The patient considered this a rash. A close-up photograph. Present for less than one week. No relevant systemic symptoms. Located on the leg and arm. Symptoms reported: itching.
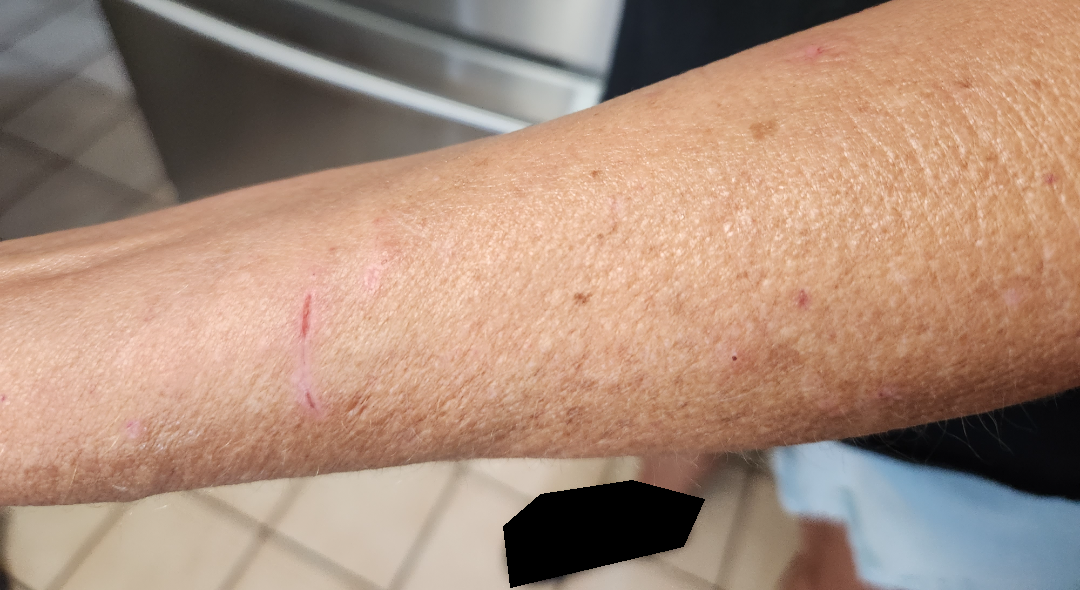differential: the favored diagnosis is Animal bite - wound; possibly Inflicted skin lesions; a more distant consideration is Eczema